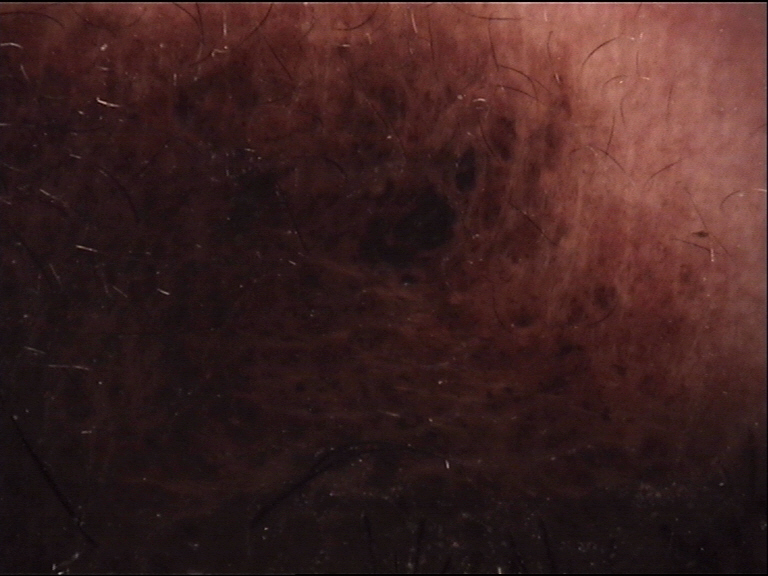<lesion>
<image>dermoscopy</image>
<diagnosis>
<name>congenital compound nevus</name>
<code>ccb</code>
<malignancy>benign</malignancy>
<super_class>melanocytic</super_class>
<confirmation>expert consensus</confirmation>
</diagnosis>
</lesion>